The photo was captured at a distance. Female contributor, age 18–29. Located on the arm.
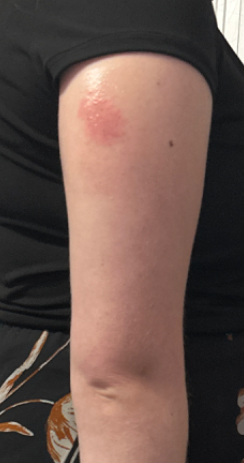The reviewing clinician's impression was: Impetigo, Injection site disorder and Allergic Contact Dermatitis were each considered, in no particular order.